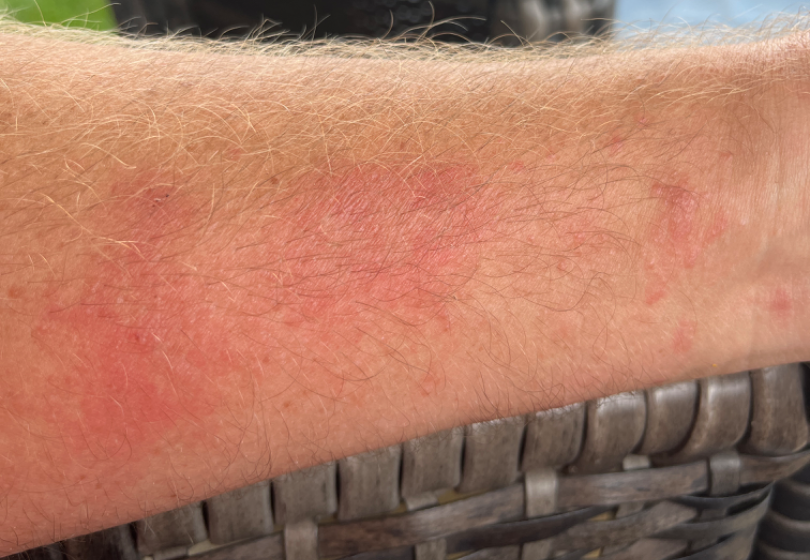assessment: unable to determine
subject: male, age 50–59
anatomic site: front of the torso and arm
photo taken: close-up